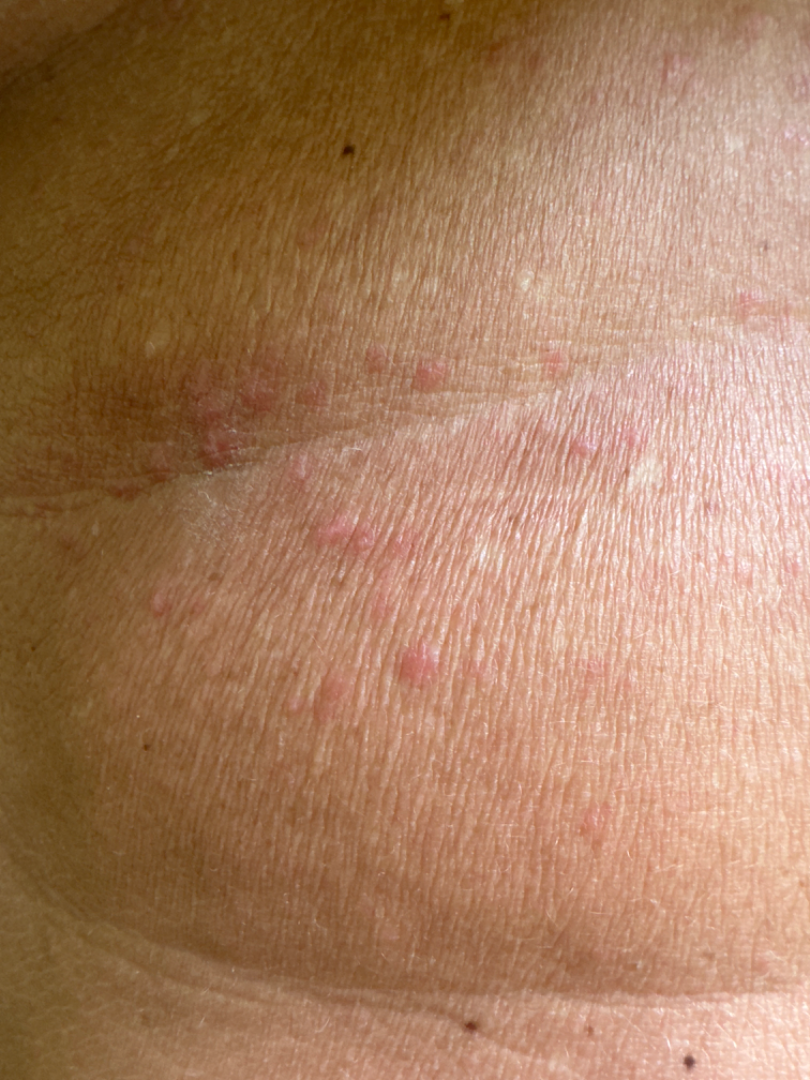This is a close-up image.
Non-clinician graders estimated MST 3 or 5.
The leading impression is Insect Bite; an alternative is Granuloma annulare; also raised was Allergic Contact Dermatitis.